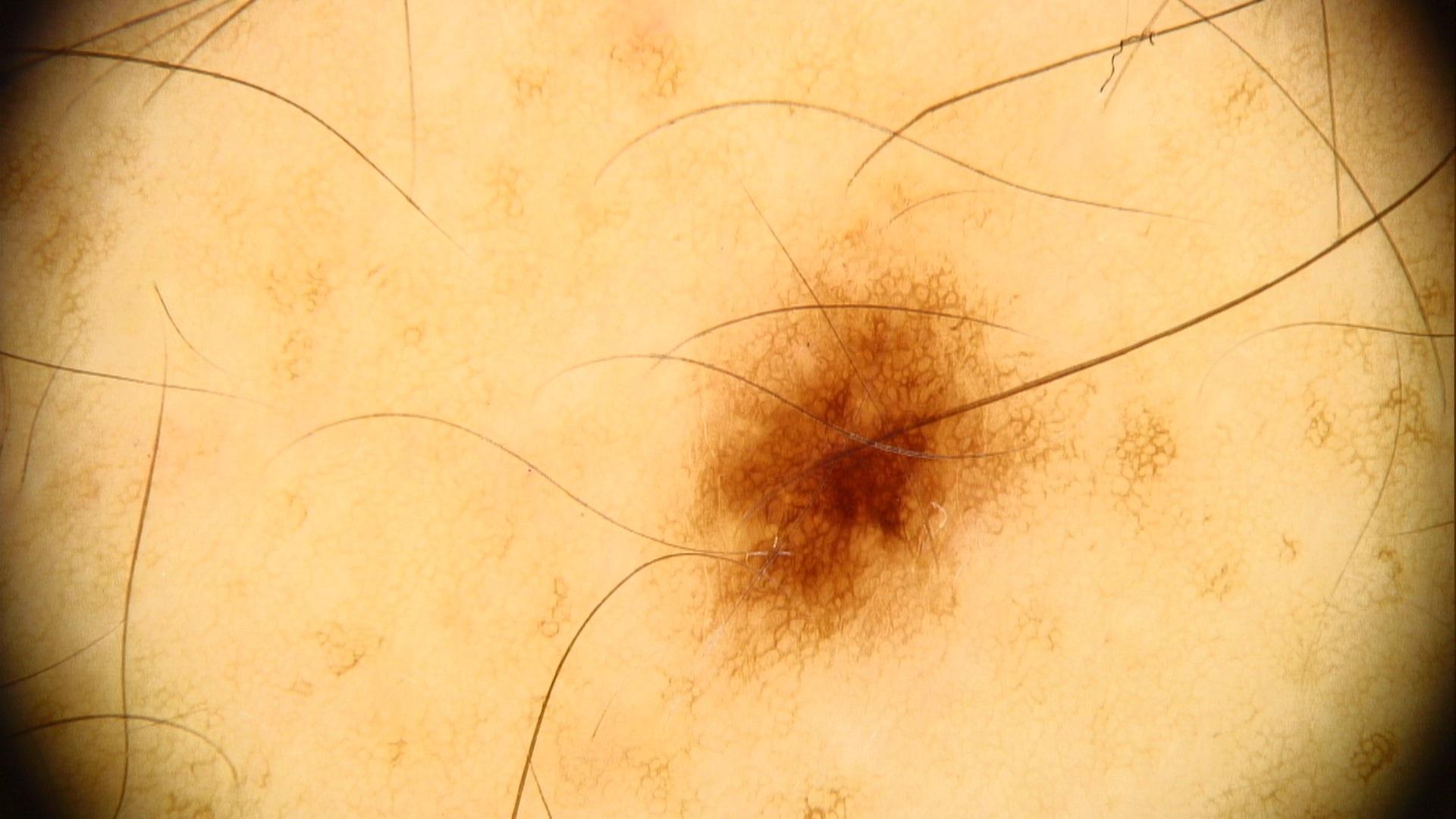A dermoscopic photograph of a skin lesion.
Clinically diagnosed as a nevus.